A skin lesion imaged with a dermatoscope.
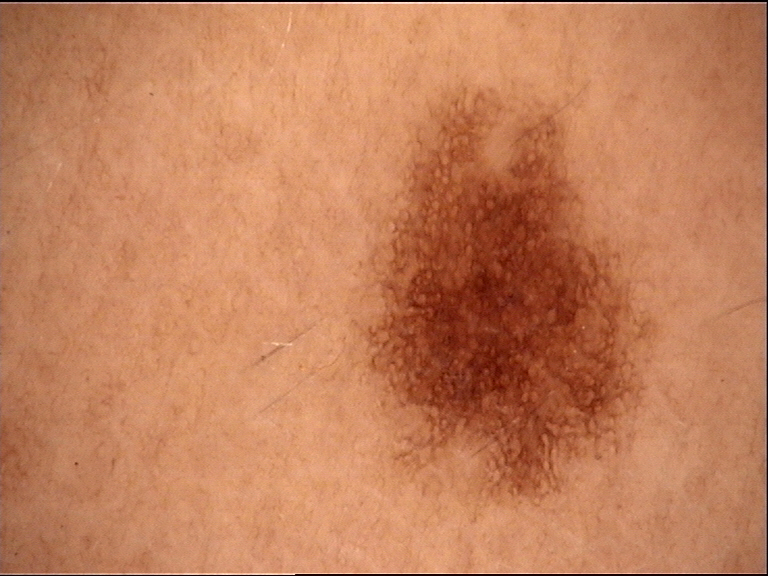The morphology is that of a banal lesion. Labeled as a junctional nevus.